Dermoscopy of a skin lesion: 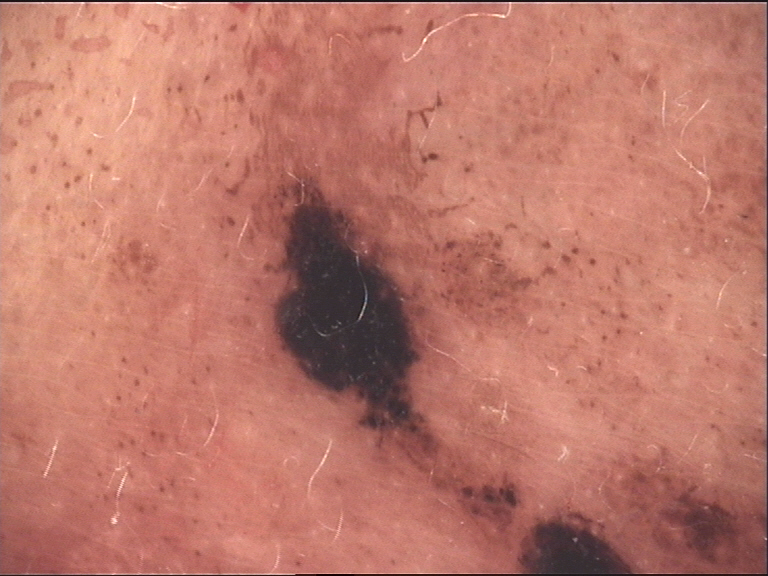The diagnostic label was a banal lesion — a congenital compound nevus.